A dermoscopic image of a skin lesion: 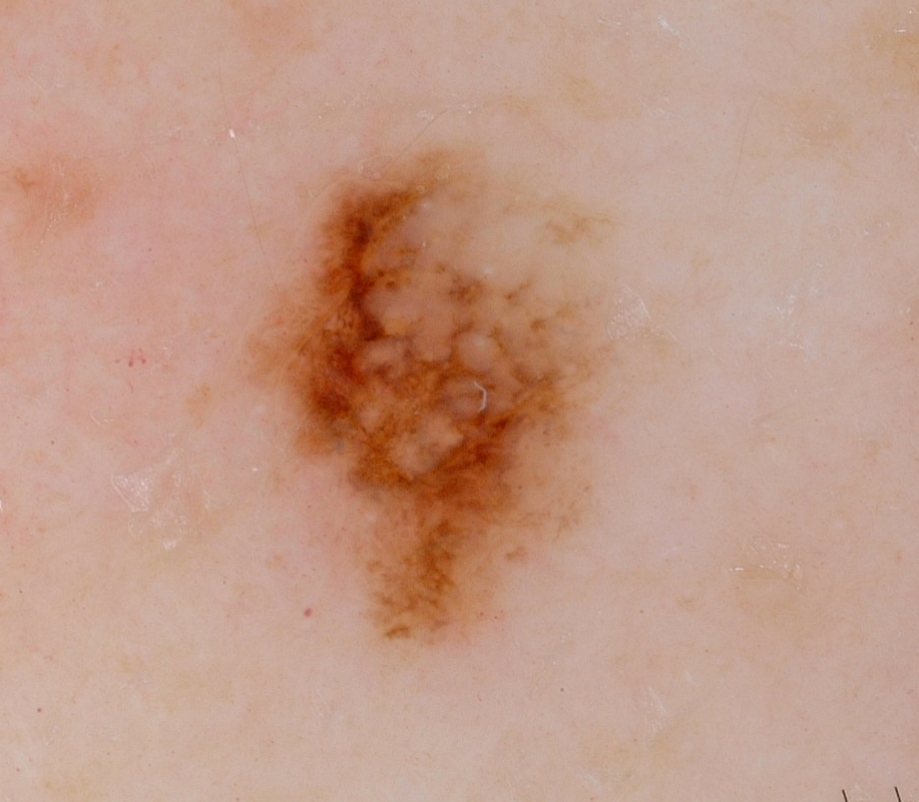Image and clinical context:
Dermoscopic review identifies no globules, milia-like cysts, pigment network, negative network, or streaks. Lesion location: (184, 135, 652, 656).
Impression:
The clinical diagnosis was a melanocytic nevus.